The photograph is a close-up of the affected area: 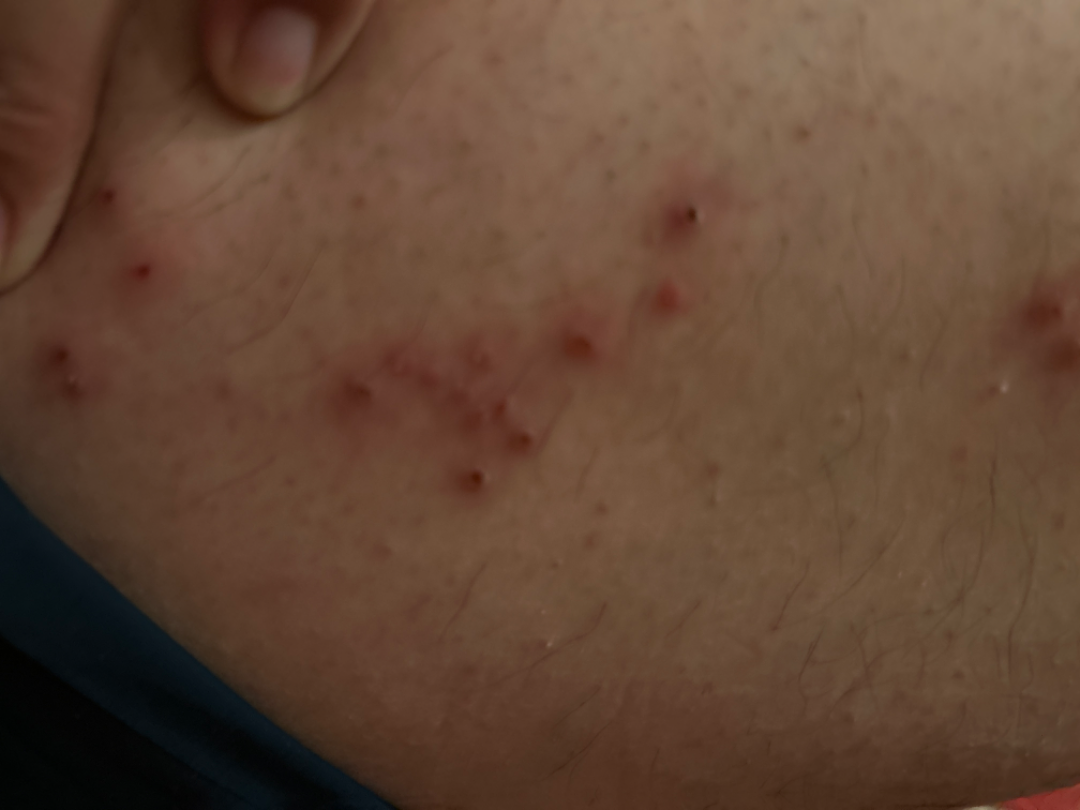differential = most likely Herpes Zoster; also raised was Impetigo.